A dermoscopic close-up of a skin lesion.
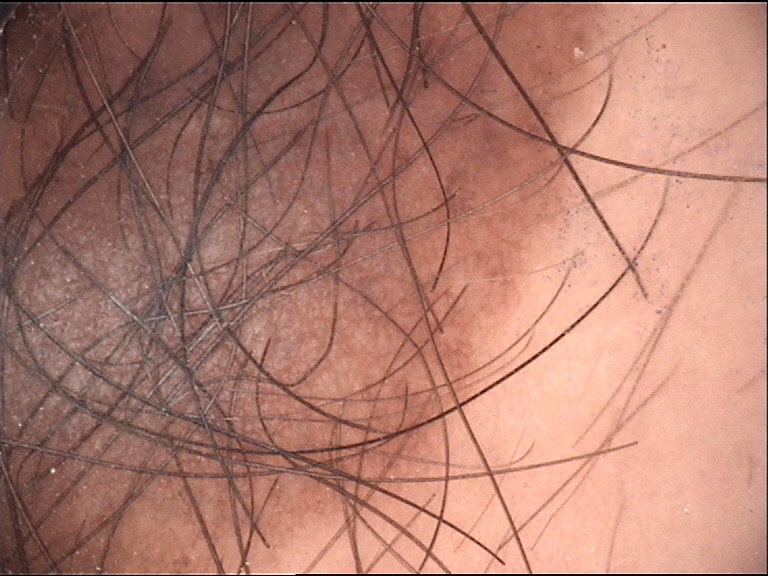Case:
The architecture is that of a banal lesion.
Impression:
Diagnosed as a congenital compound nevus.